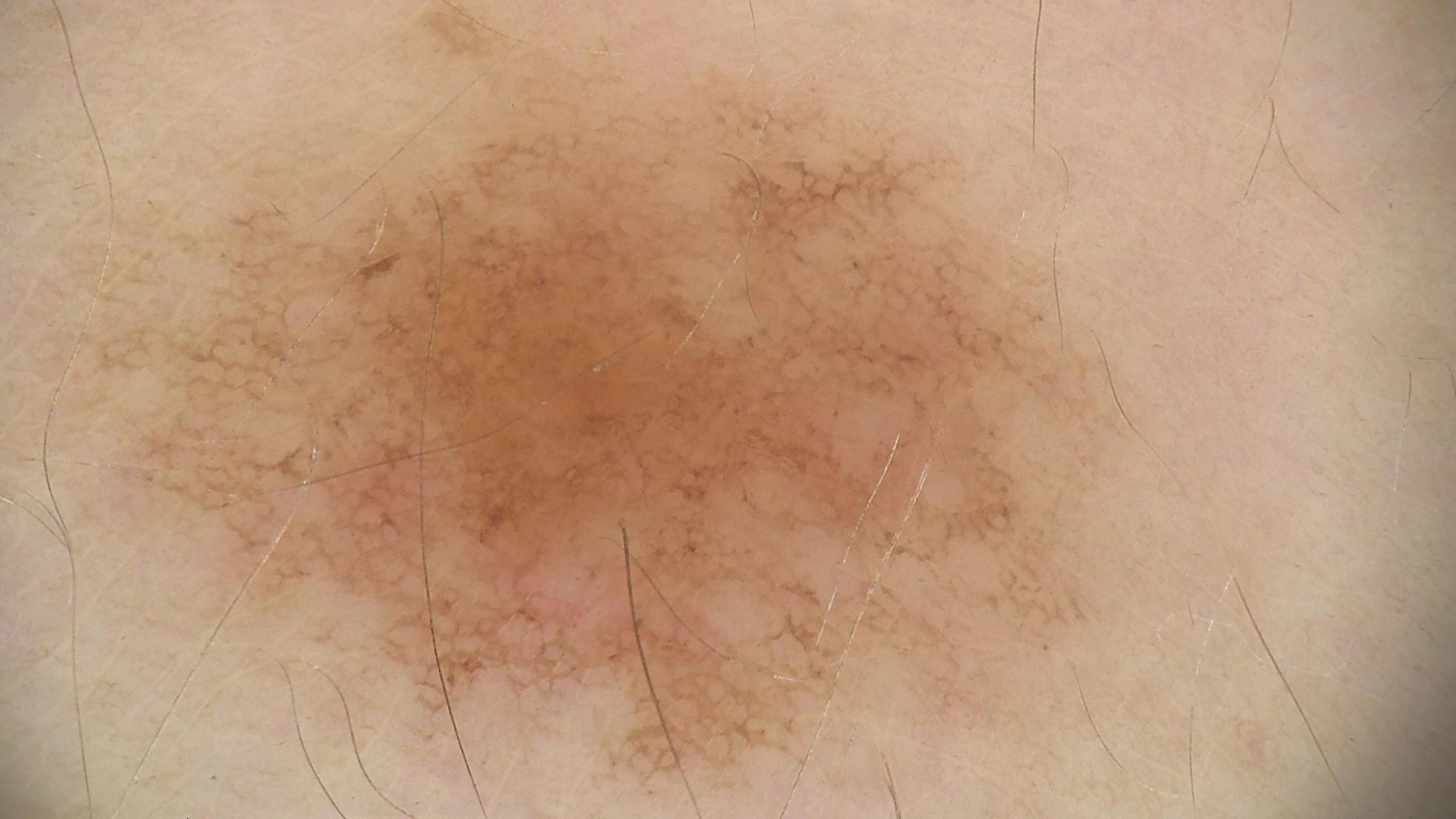Case:
– label: dysplastic junctional nevus (expert consensus)